The patient says their skin reddens with sun exposure. On a questionnaire the patient reported a personal history of cancer. A male patient aged 78. A clinical close-up of a skin lesion. Few moles overall by the patient's own estimate — 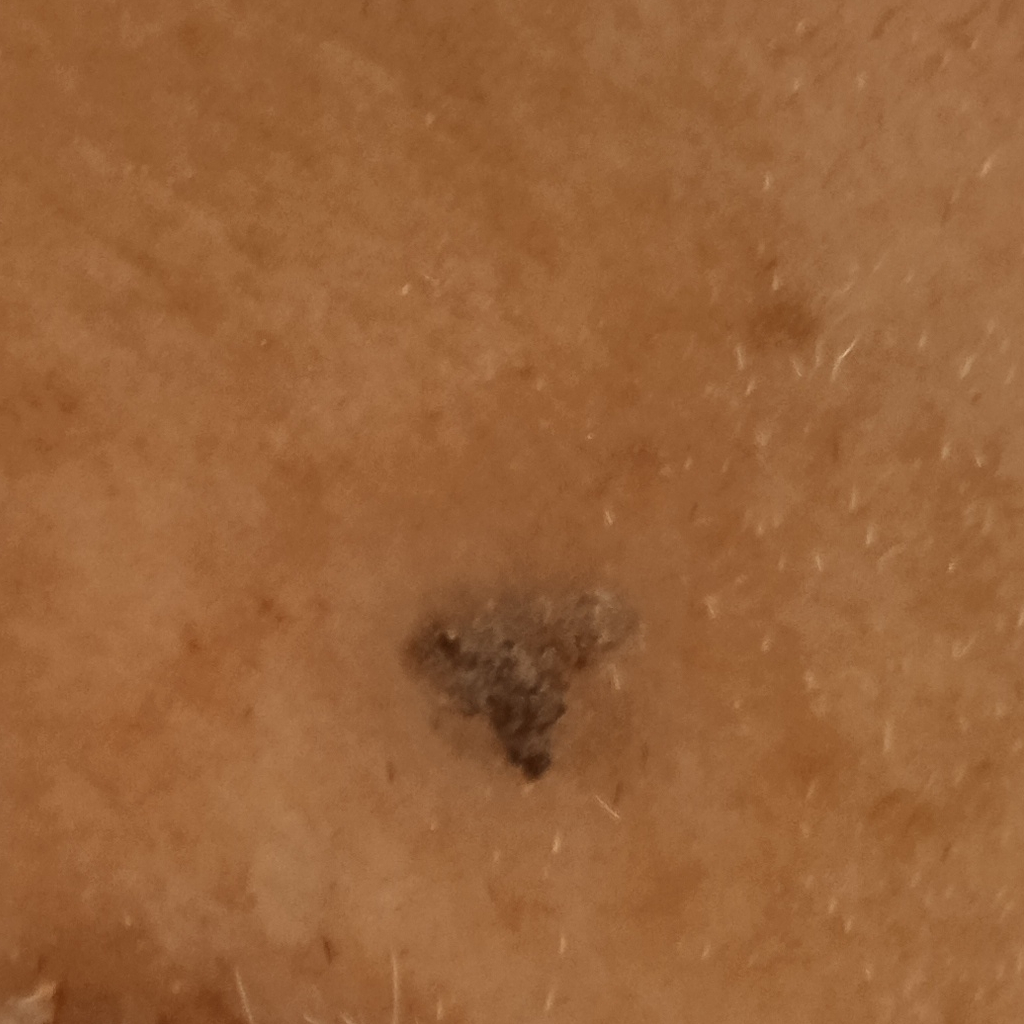The lesion is located on the face.
The lesion measures approximately 10.5 mm.
The lesion was assessed as a seborrheic keratosis.